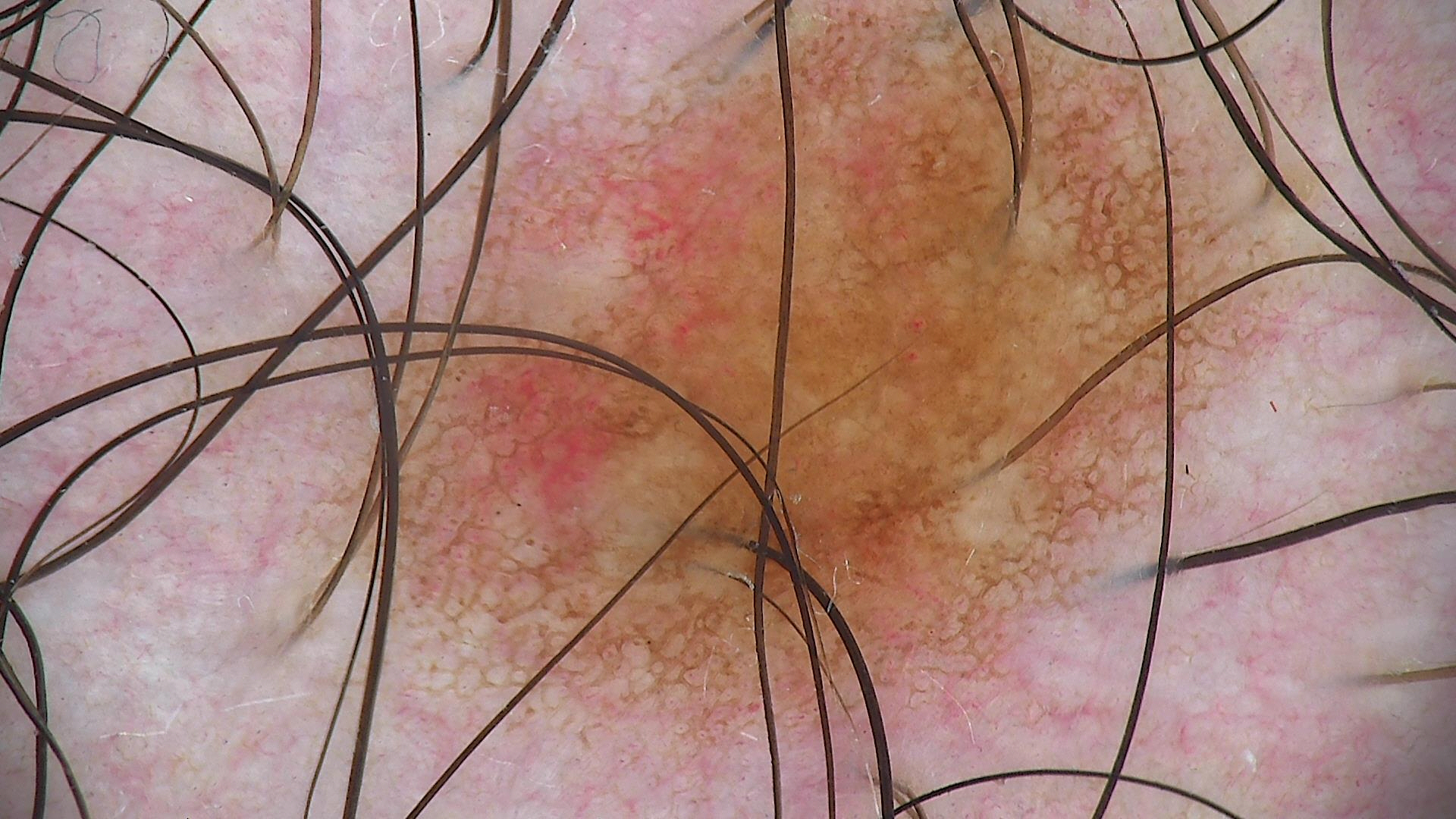image = dermatoscopy | diagnostic label = dysplastic junctional nevus (expert consensus).